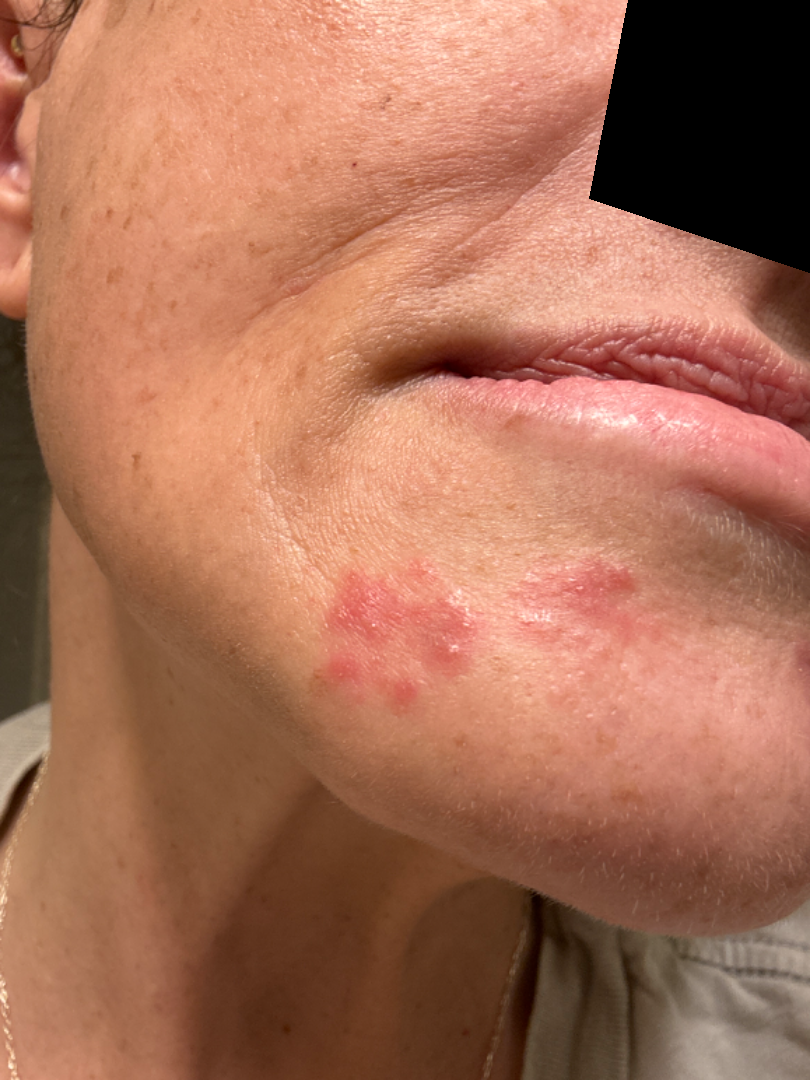Clinical context:
Skin tone: lay reviewers estimated Monk Skin Tone 3 (US pool) or 2 (India pool). The patient considered this a rash. Texture is reported as raised or bumpy. The head or neck is involved. The patient is 50–59, female. The lesion is associated with bothersome appearance. The condition has been present for one to four weeks. This is a close-up image.
Assessment:
The reviewing clinician's impression was: Perioral Dermatitis (100%).